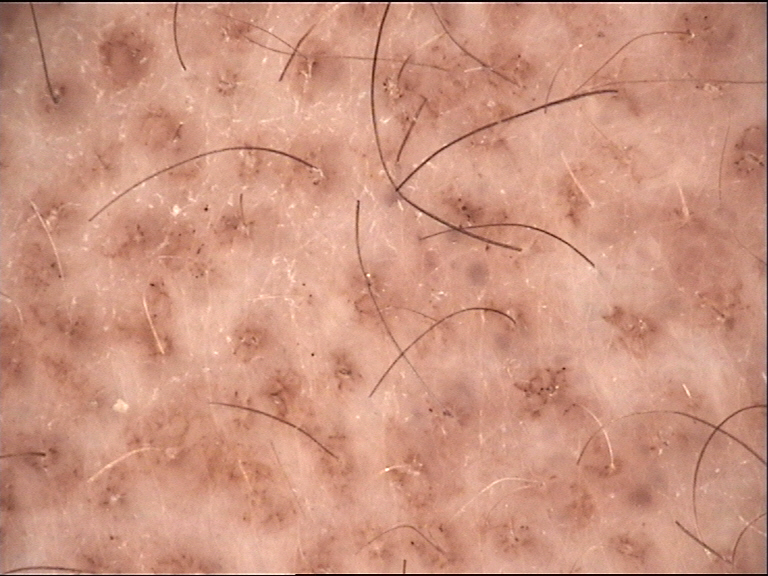Q: What was the diagnostic impression?
A: congenital compound nevus (expert consensus)